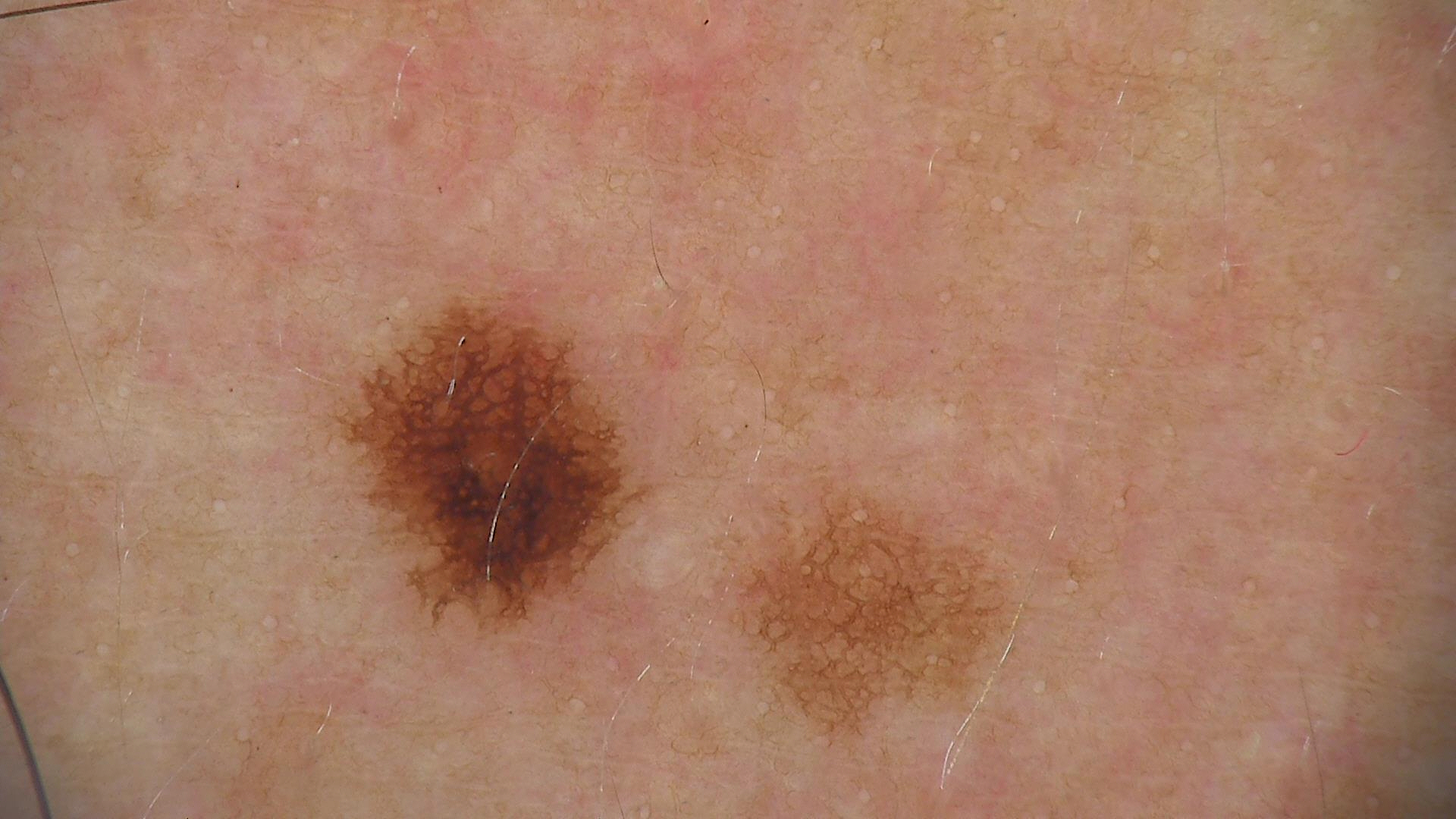Q: What is this lesion?
A: dysplastic junctional nevus (expert consensus)